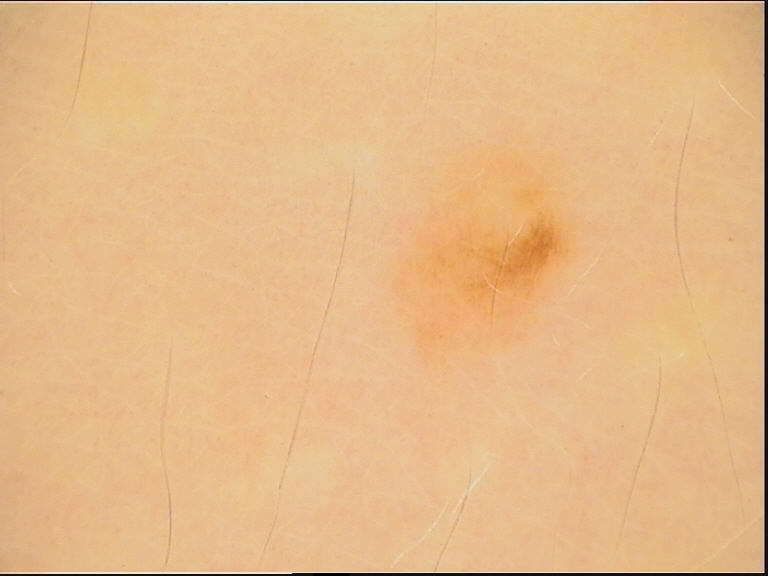image: dermoscopy; class: junctional nevus (expert consensus).